The chart records pesticide exposure, no tobacco use, and no prior skin cancer (patient or family). Recorded as skin type II. A clinical photo of a skin lesion taken with a smartphone: 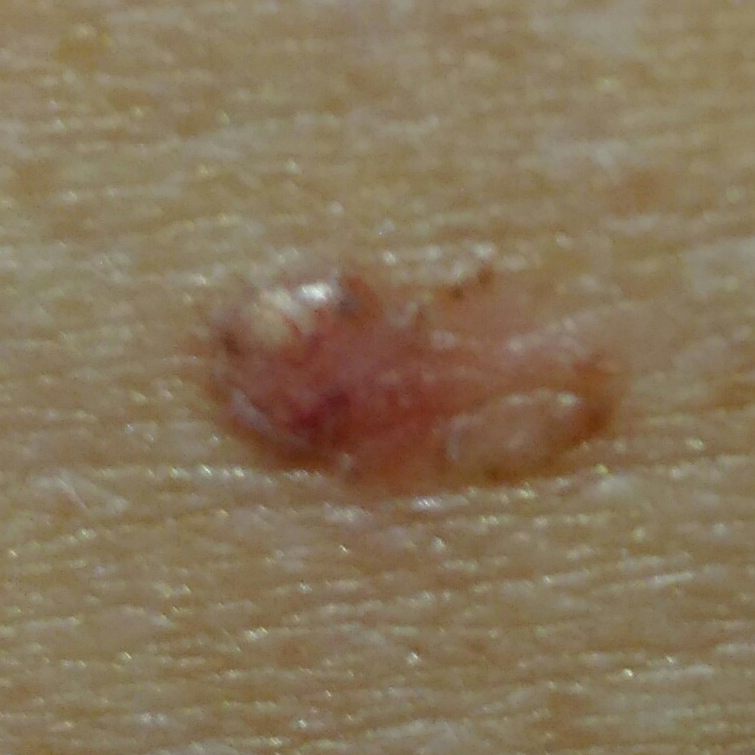The lesion involves the back. The lesion measures approximately 10 × 5 mm. The patient reports that the lesion has grown, is elevated, and itches. The biopsy diagnosis was a malignant lesion — a basal cell carcinoma.